A dermoscopic close-up of a skin lesion.
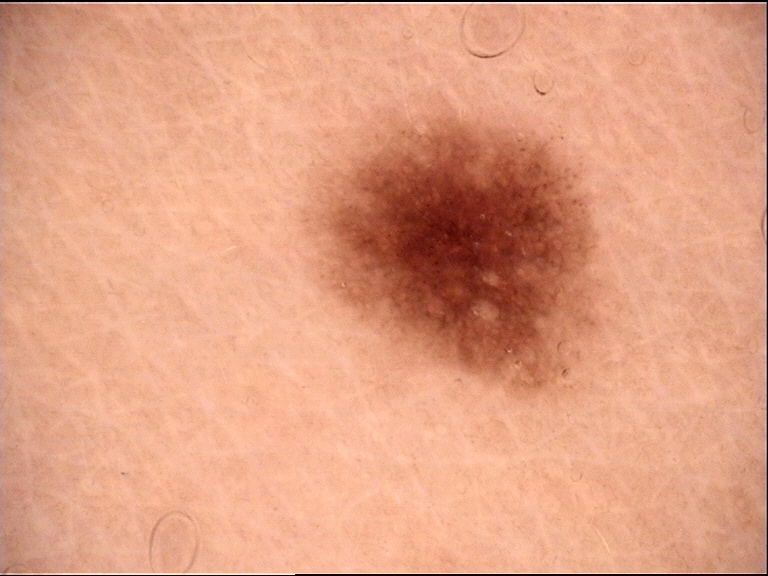{
  "diagnosis": {
    "name": "dysplastic junctional nevus",
    "code": "jd",
    "malignancy": "benign",
    "super_class": "melanocytic",
    "confirmation": "expert consensus"
  }
}